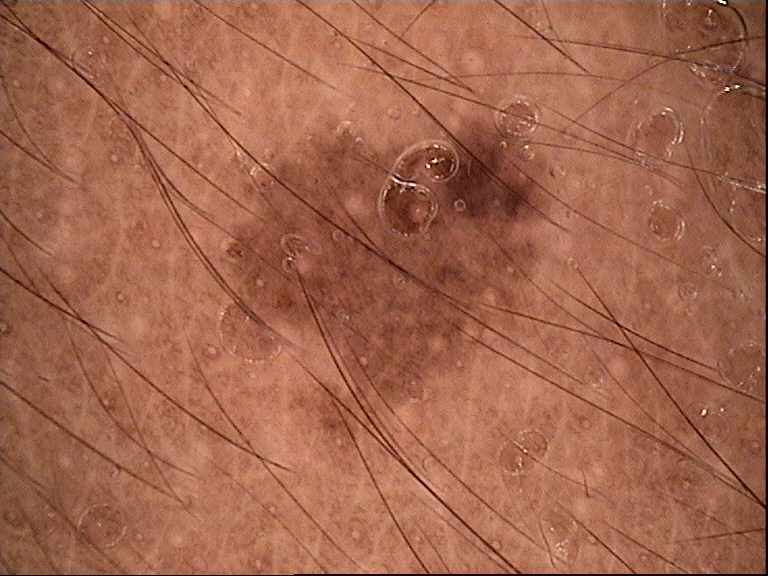Labeled as a dysplastic junctional nevus.